A moderate number of moles by the patient's own estimate; by self-report, a history of sunbed use; a skin lesion imaged with a dermatoscope; a female patient age 47; acquired for a research image collection, with no referral diagnosis.
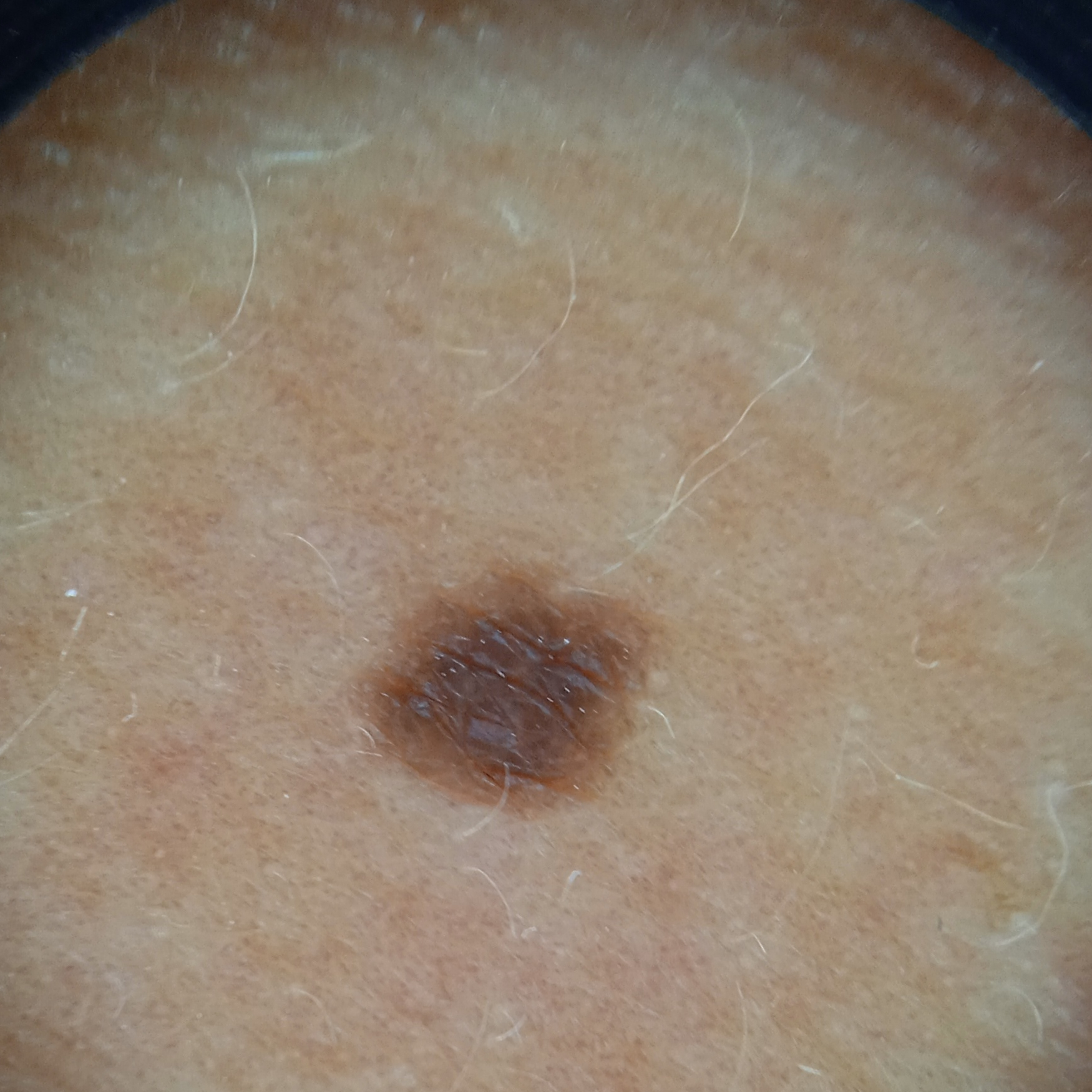The lesion measures approximately 3.3 mm.
The consensus diagnosis for this lesion was a melanocytic nevus.